A dermoscopic view of a skin lesion.
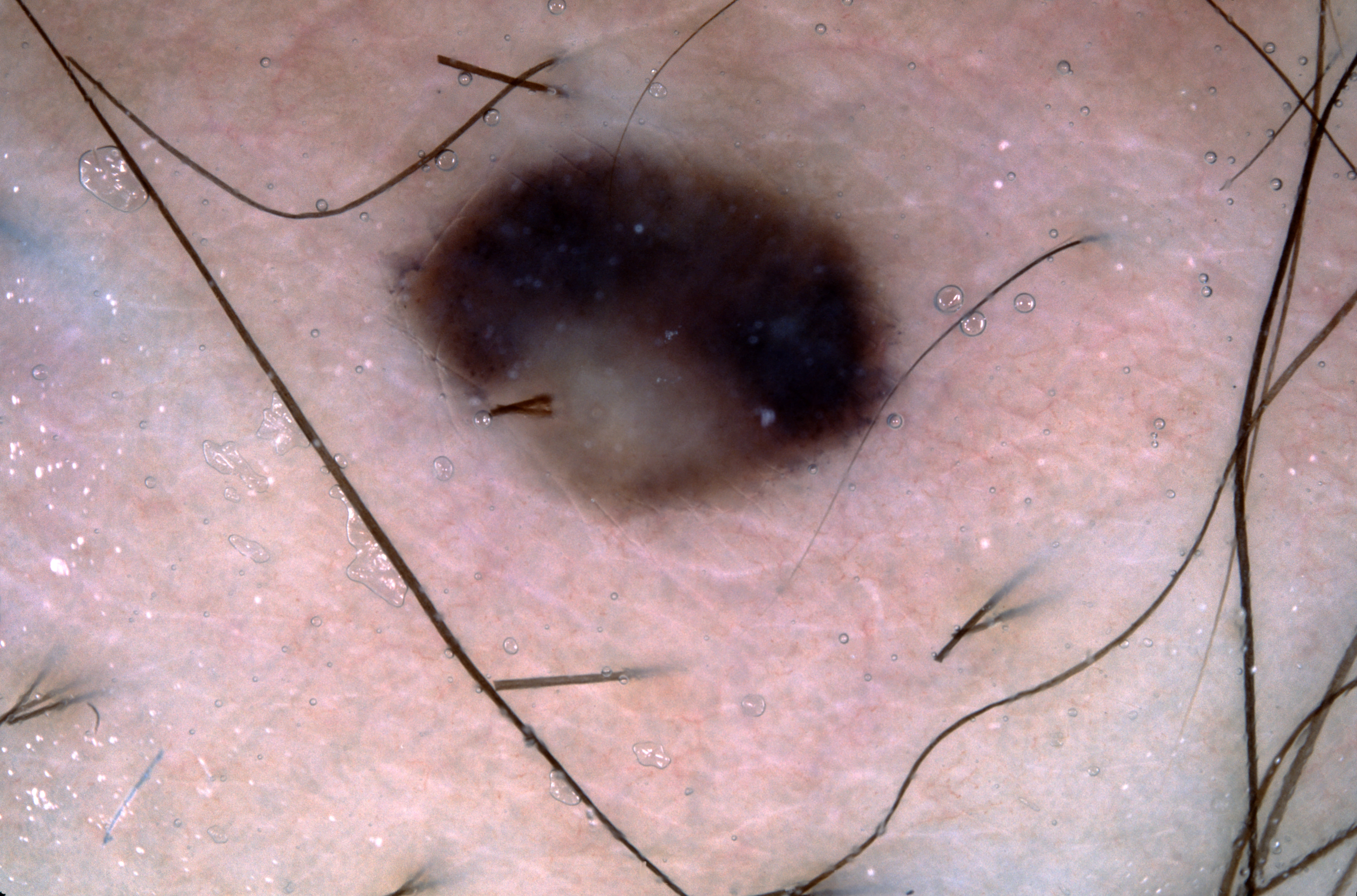Findings:
* lesion location · x1=403 y1=154 x2=891 y2=518
* diagnostic label · a melanocytic nevus, a benign skin lesion